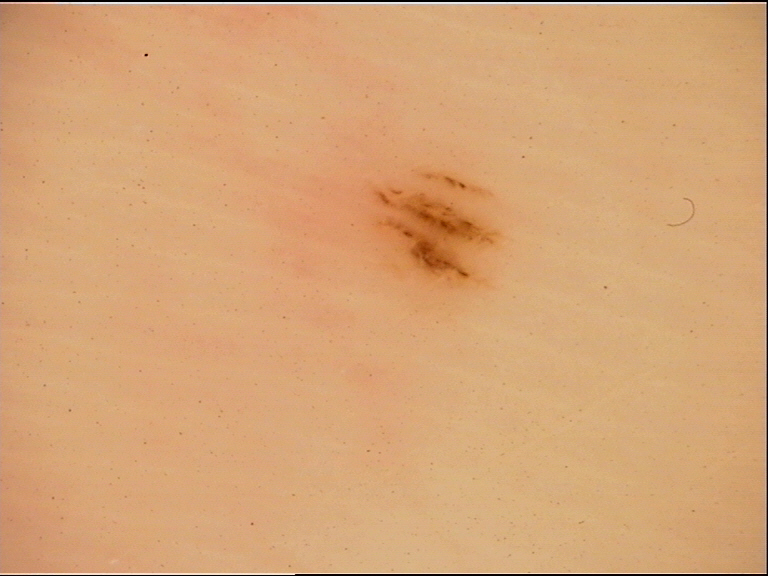A dermoscopy image of a single skin lesion. The architecture is that of a banal lesion. The diagnostic label was an acral junctional nevus.